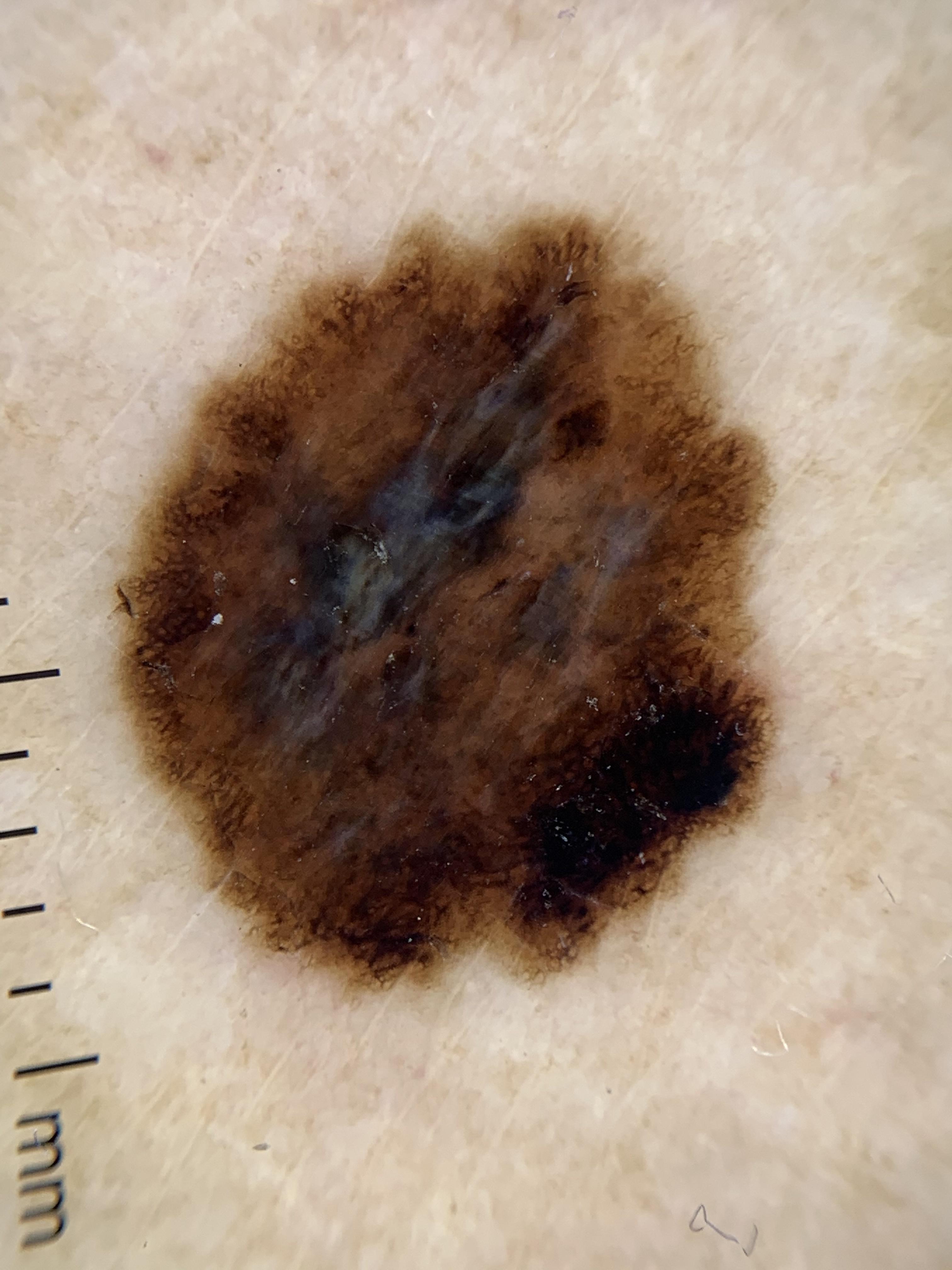Recorded as skin type III. The chart records a previous melanoma. A dermatoscopic image of a skin lesion. A female patient aged approximately 75. Histopathological examination showed a skin cancer — a melanoma.